A dermoscopic view of a skin lesion.
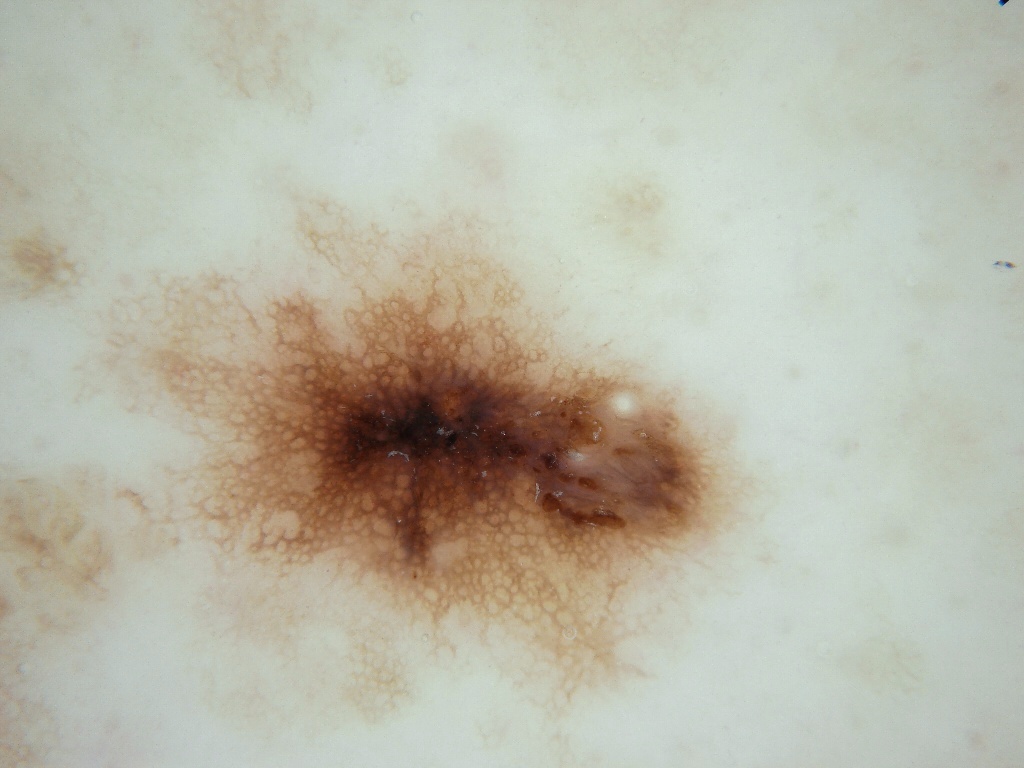Case summary:
The visible lesion spans left=70, top=191, right=767, bottom=727. On dermoscopy, the lesion shows pigment network and milia-like cysts.
Assessment:
Expert review diagnosed this as a melanocytic nevus, a benign skin lesion.